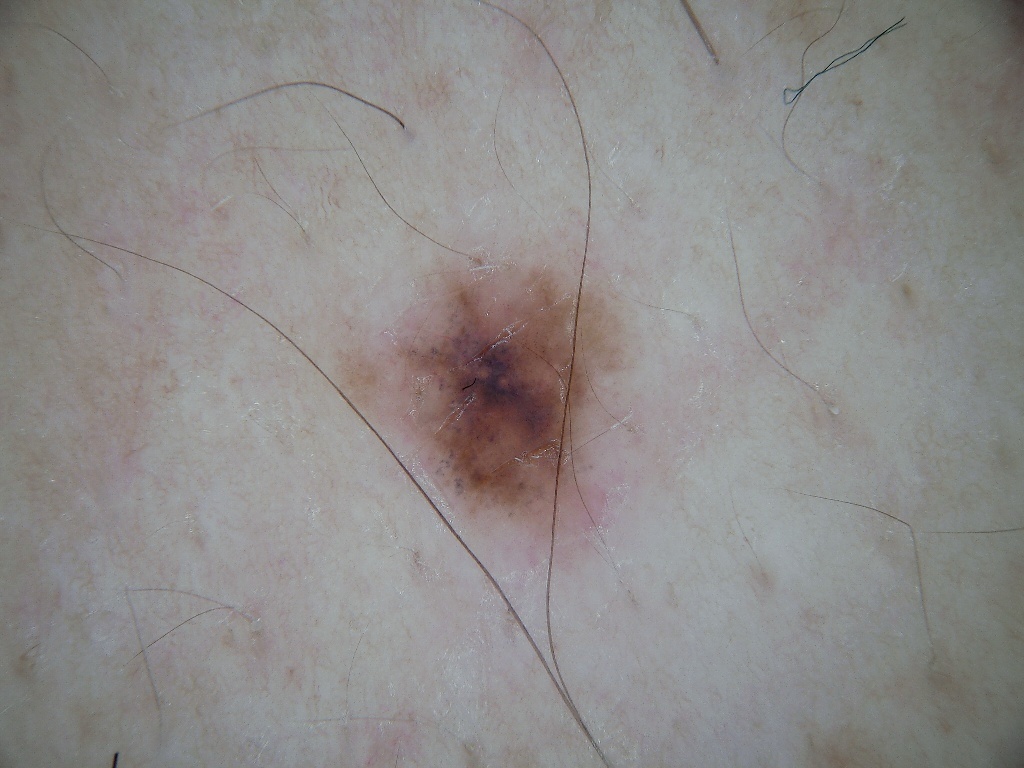subject: male, approximately 40 years of age; modality: dermatoscopic image of a skin lesion; lesion location: <box>327, 229, 648, 591</box>; absent dermoscopic findings: globules, streaks, negative network, milia-like cysts, and pigment network; impression: a melanocytic nevus, a benign skin lesion.